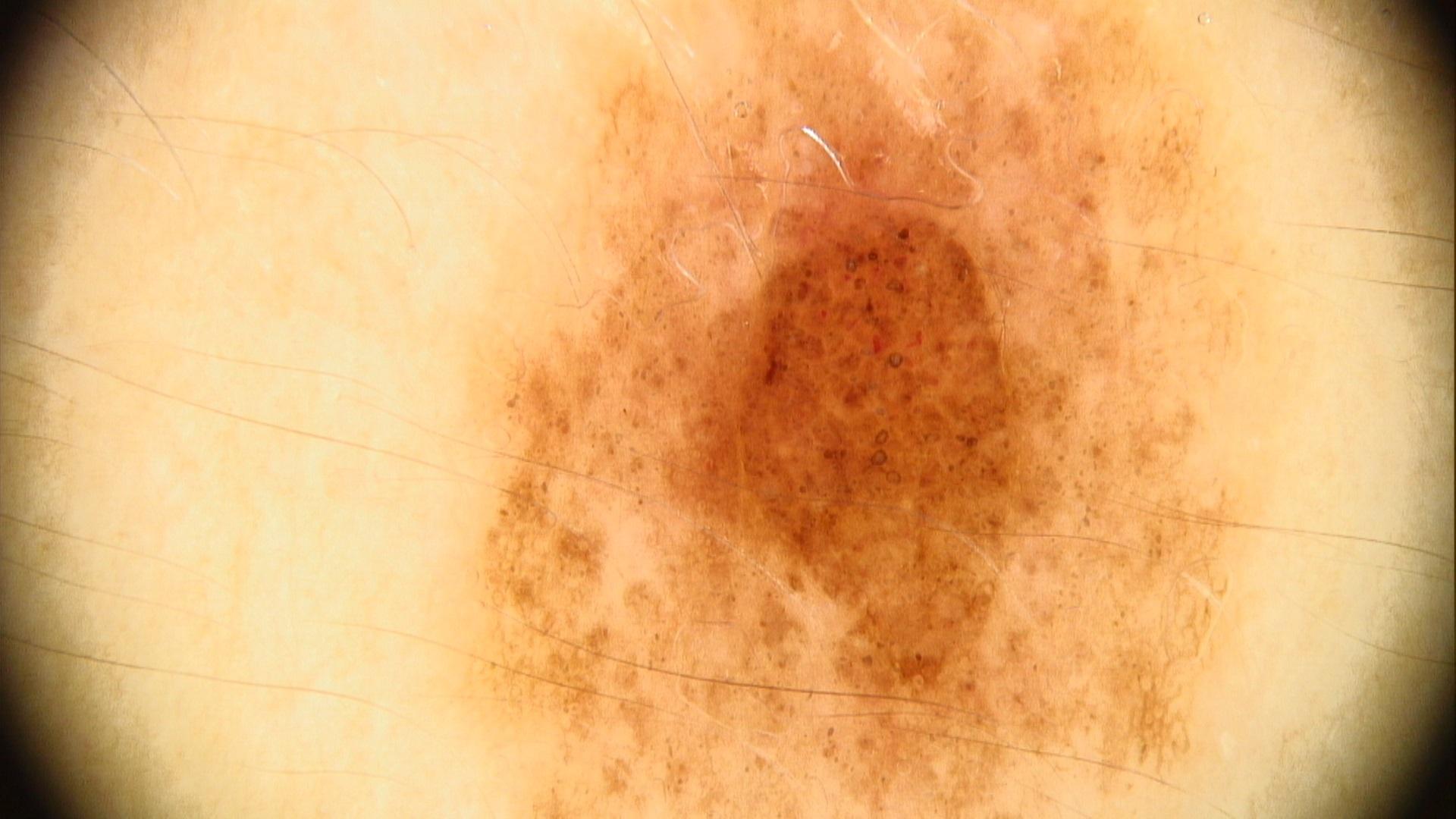Q: What is the imaging modality?
A: contact-polarized dermoscopy
Q: What are the patient's age and sex?
A: female, about 30 years old
Q: What does the history note?
A: no melanoma in first-degree relatives and no previous melanoma
Q: Where on the body is the lesion?
A: the trunk
Q: What was the clinical impression?
A: Nevus